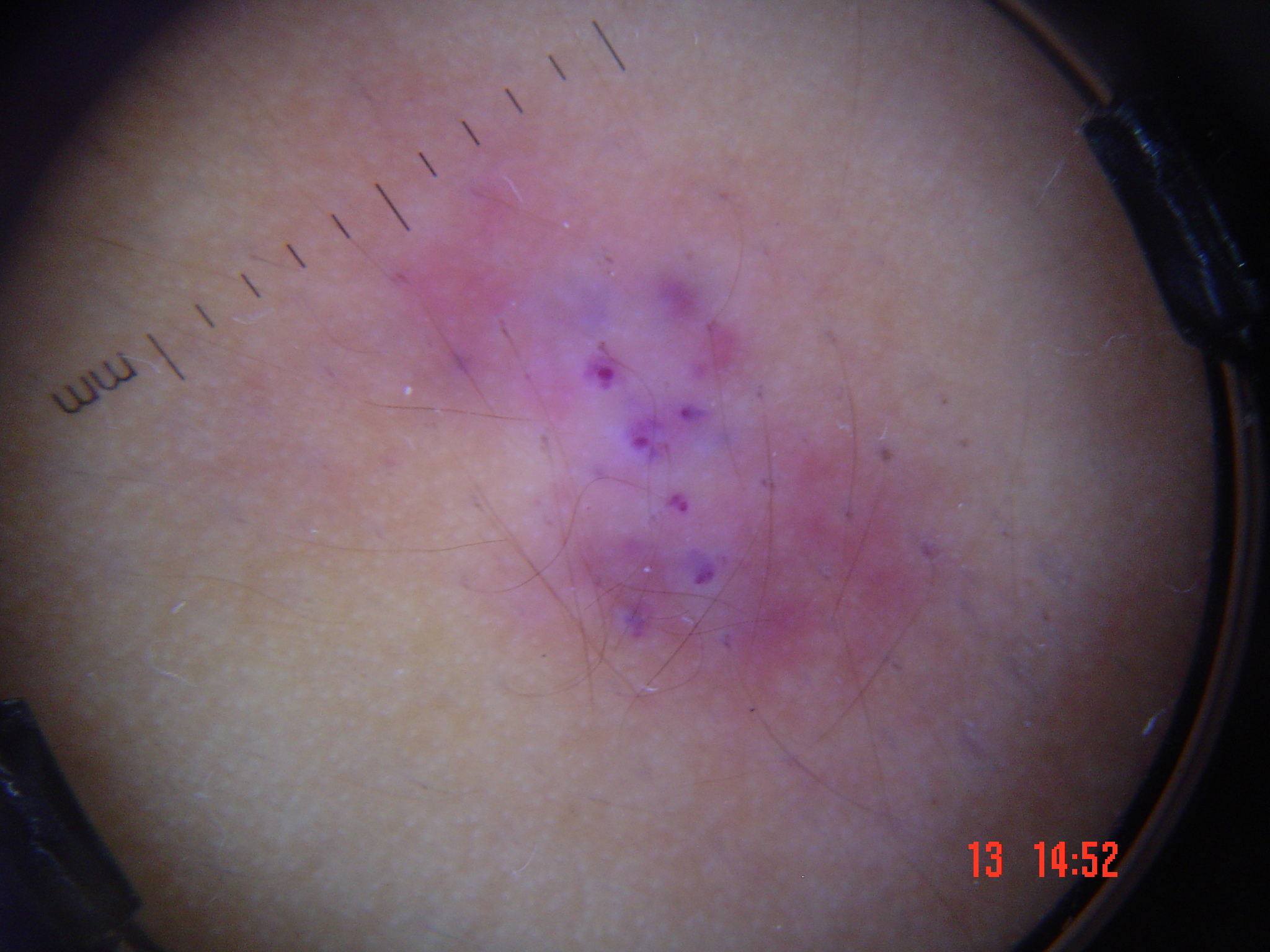Classified as a benign lesion — an angiokeratoma.